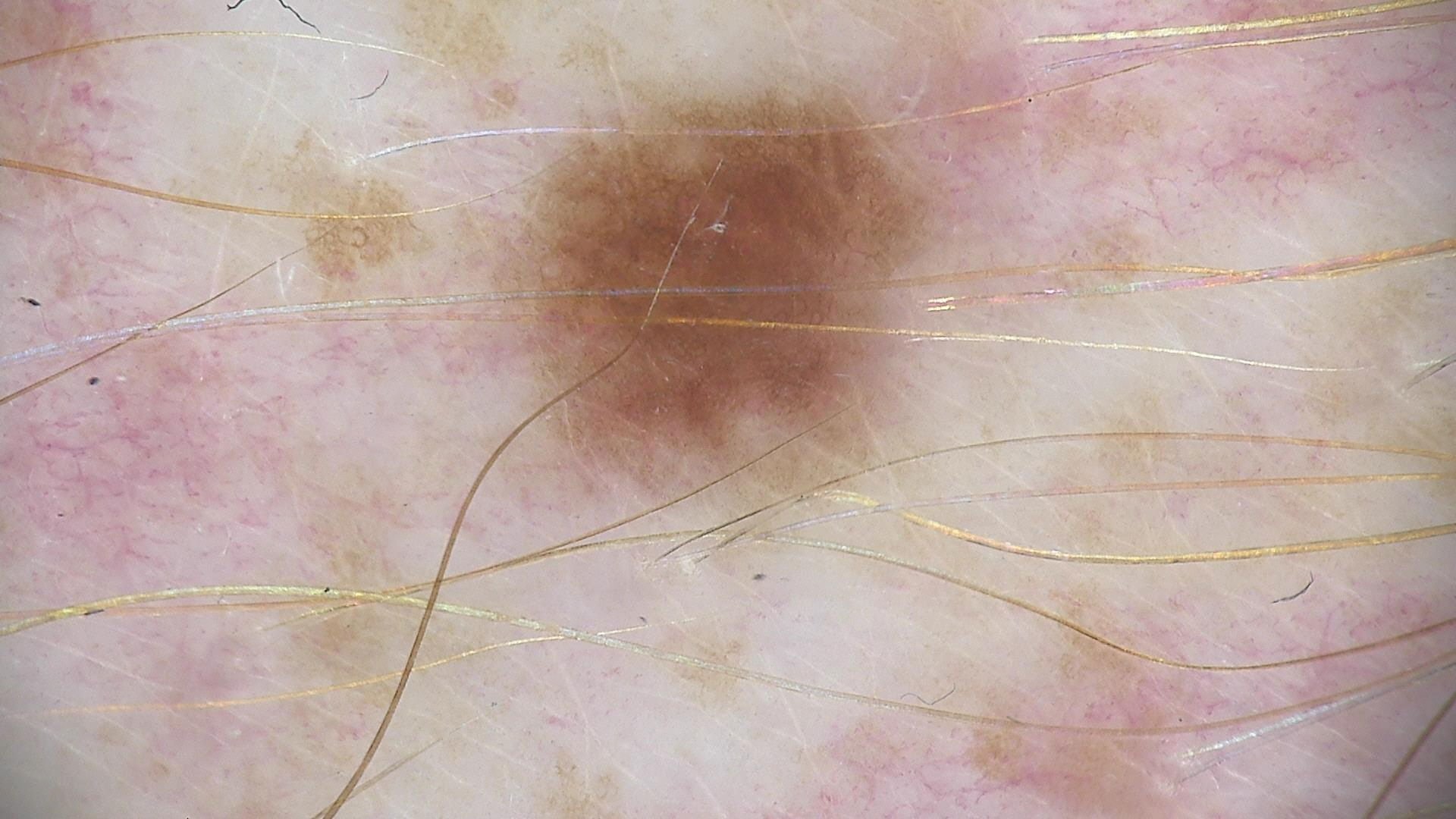label: dysplastic junctional nevus (expert consensus).